Close-up view:
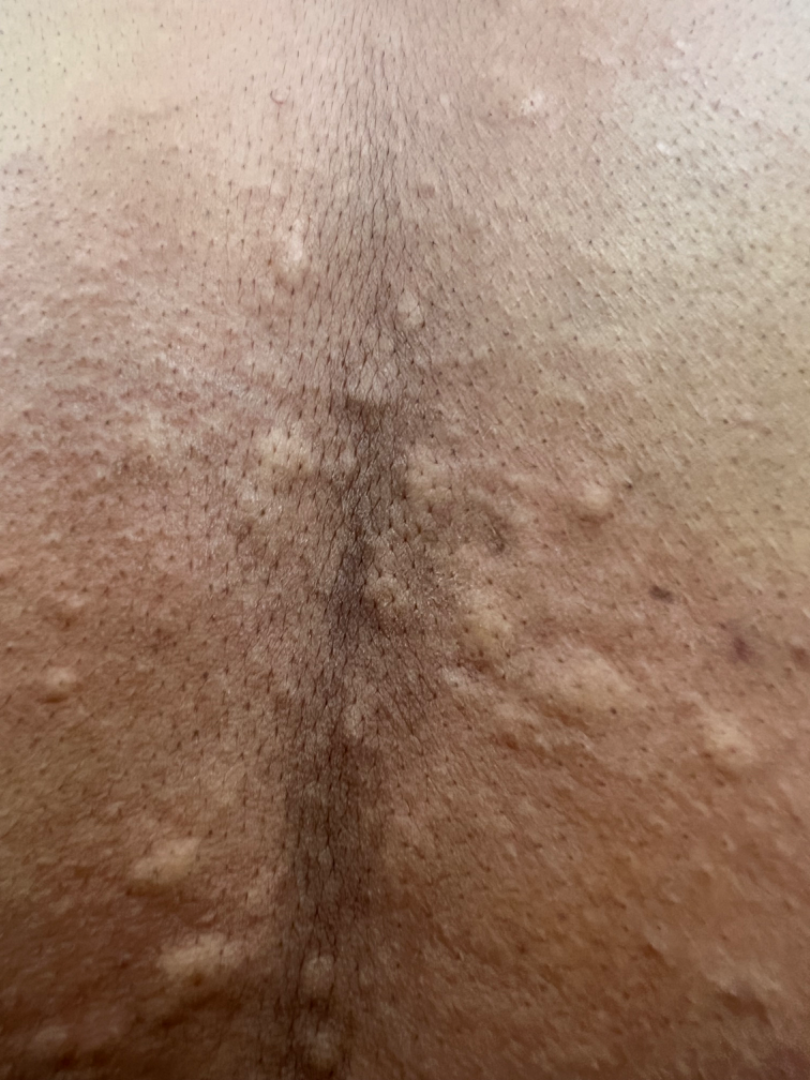onset: about one day | self-categorized as: acne | described texture: raised or bumpy | symptoms: itching | impression: the favored diagnosis is Urticaria; with consideration of Allergic Contact Dermatitis.